The leg is involved · the lesion is described as rough or flaky · no relevant lesion symptoms reported · the photo was captured at an angle · present for one to four weeks: 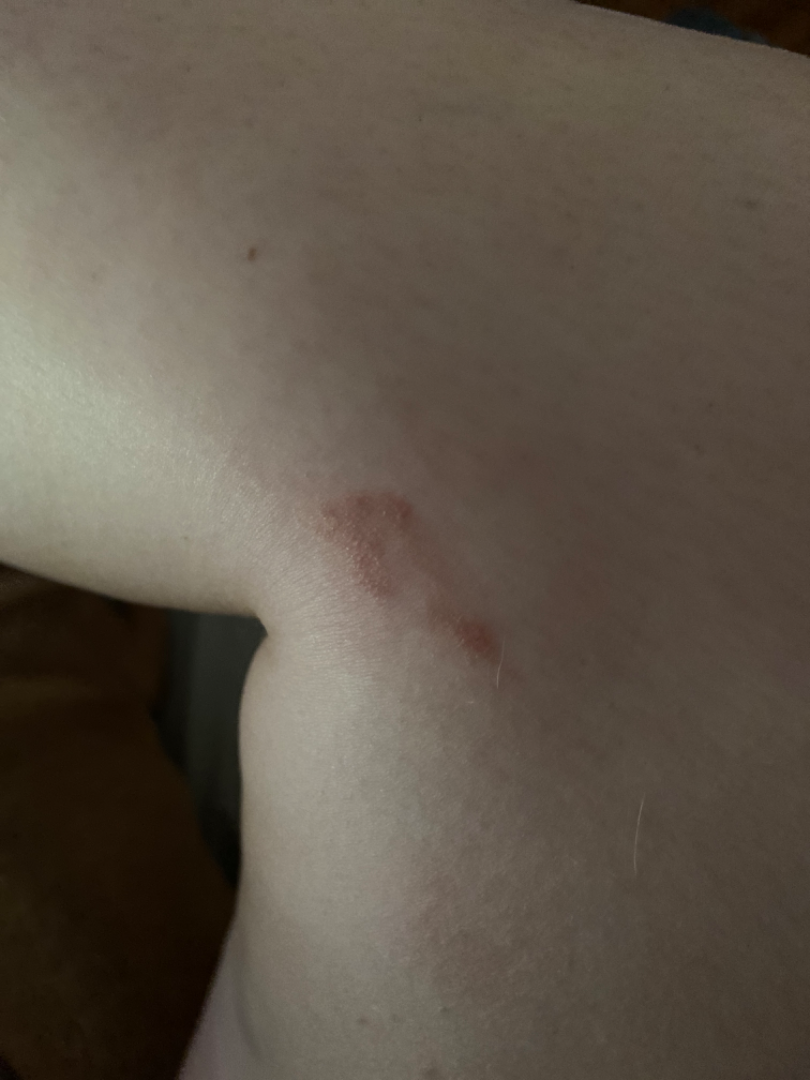The condition could not be reliably identified from the image.